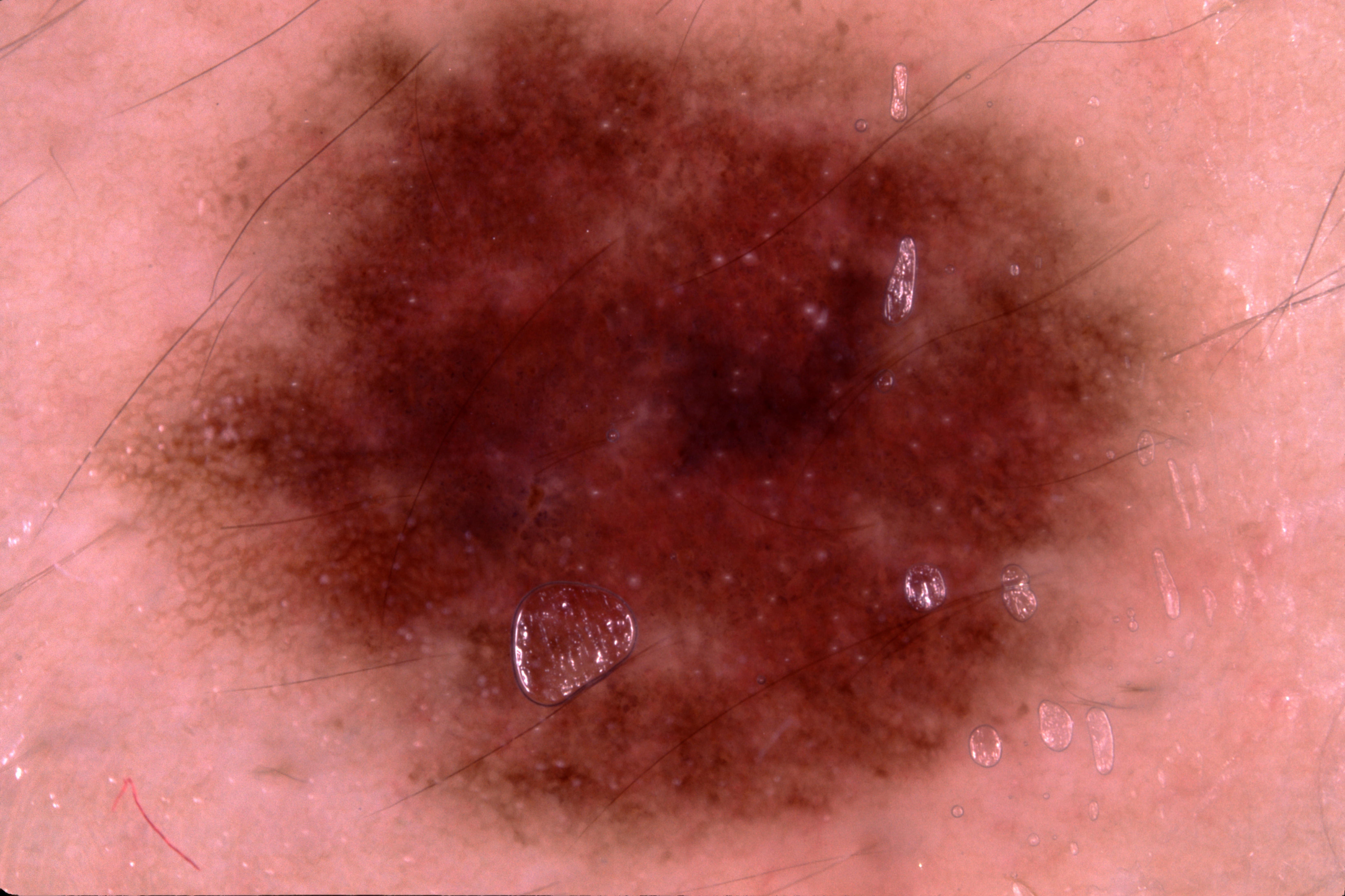A skin lesion imaged with a dermatoscope. A male subject, aged 23 to 27. In (x1, y1, x2, y2) order, the lesion is bounded by (108, 0, 1215, 895). The lesion takes up about 58% of the image. Dermoscopy demonstrates pigment network and milia-like cysts, with no negative network or streaks. The diagnostic assessment was a melanocytic nevus, a benign lesion.